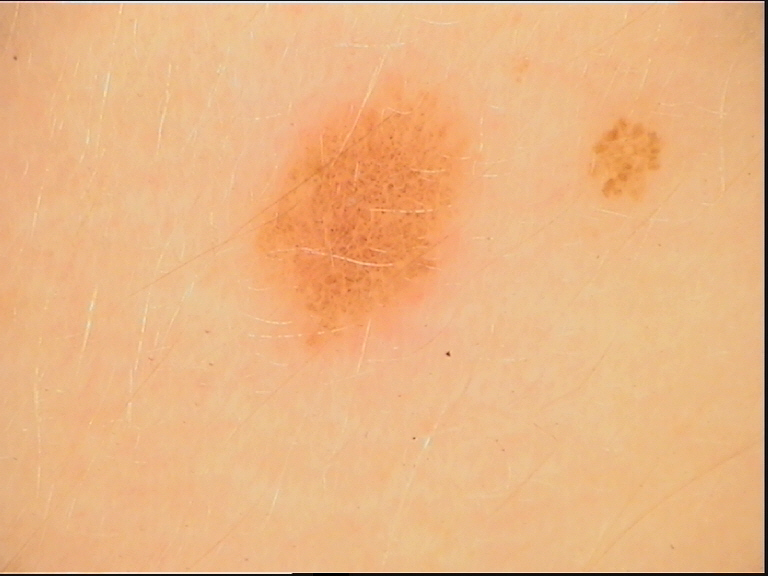A dermatoscopic image of a skin lesion.
Consistent with a benign lesion — a dysplastic junctional nevus.